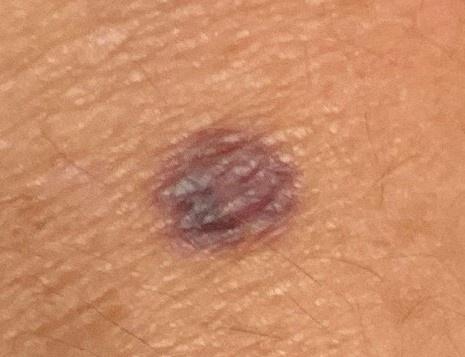Image and clinical context: The patient was assessed as Fitzpatrick skin type II. A clinical photograph showing a skin lesion in context. A female subject roughly 60 years of age. Assessment: The clinical impression was a benign vascular lesion.